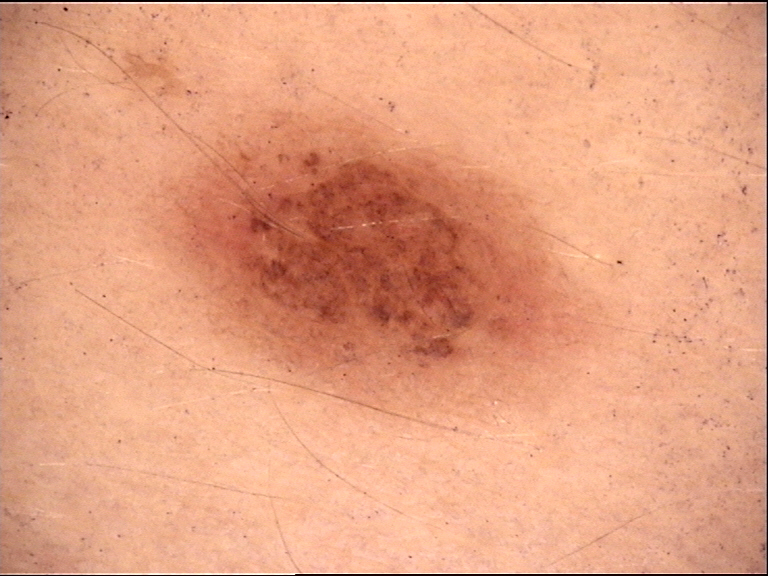Diagnosed as a compound nevus.